Imaged for a research study, with no referral diagnosis recorded; a male patient 72 years old; dermoscopy of a skin lesion.
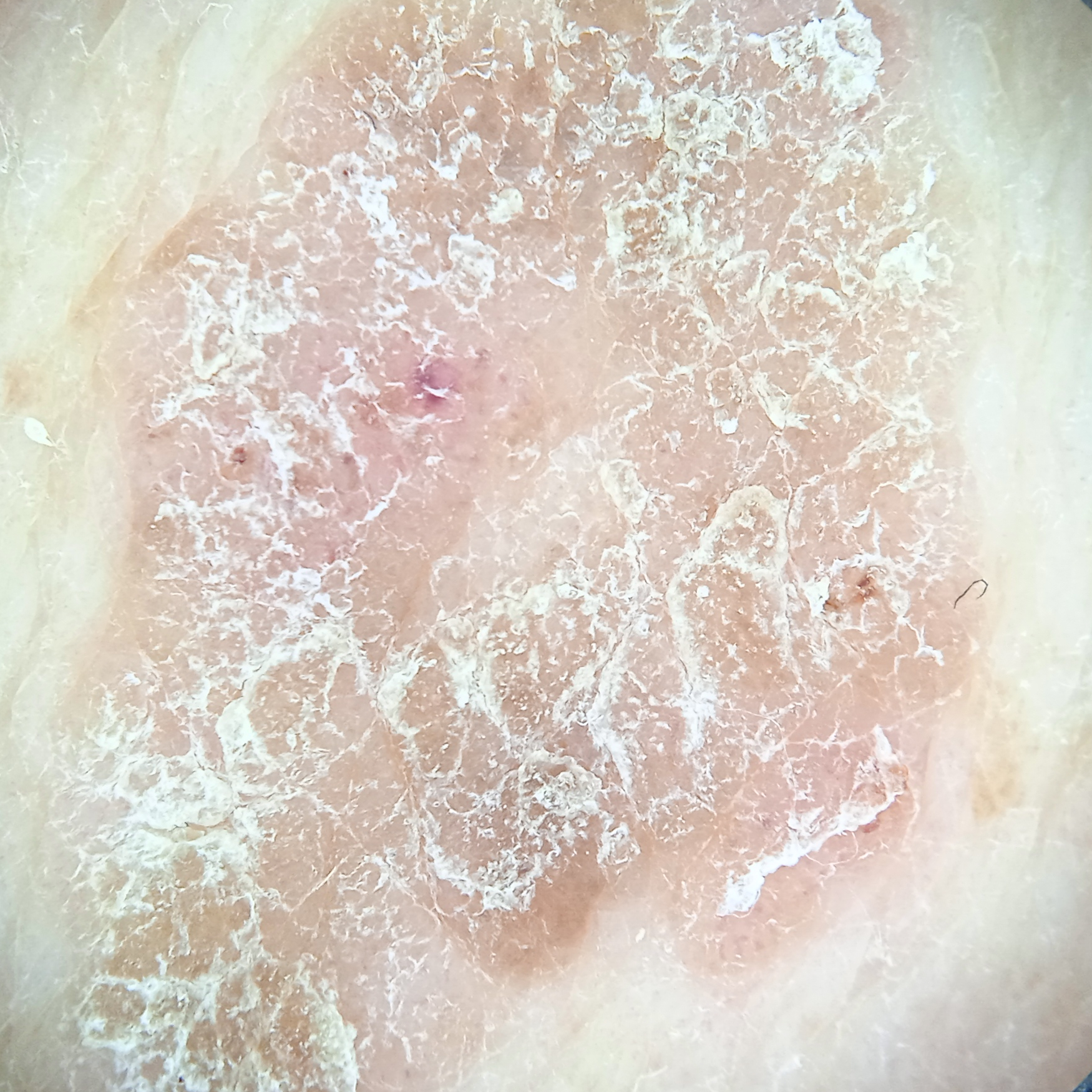body site = the back
size = 16.5 mm
diagnosis = seborrheic keratosis (dermatologist consensus)